The lesion involves the back of the torso · the photograph is a close-up of the affected area.
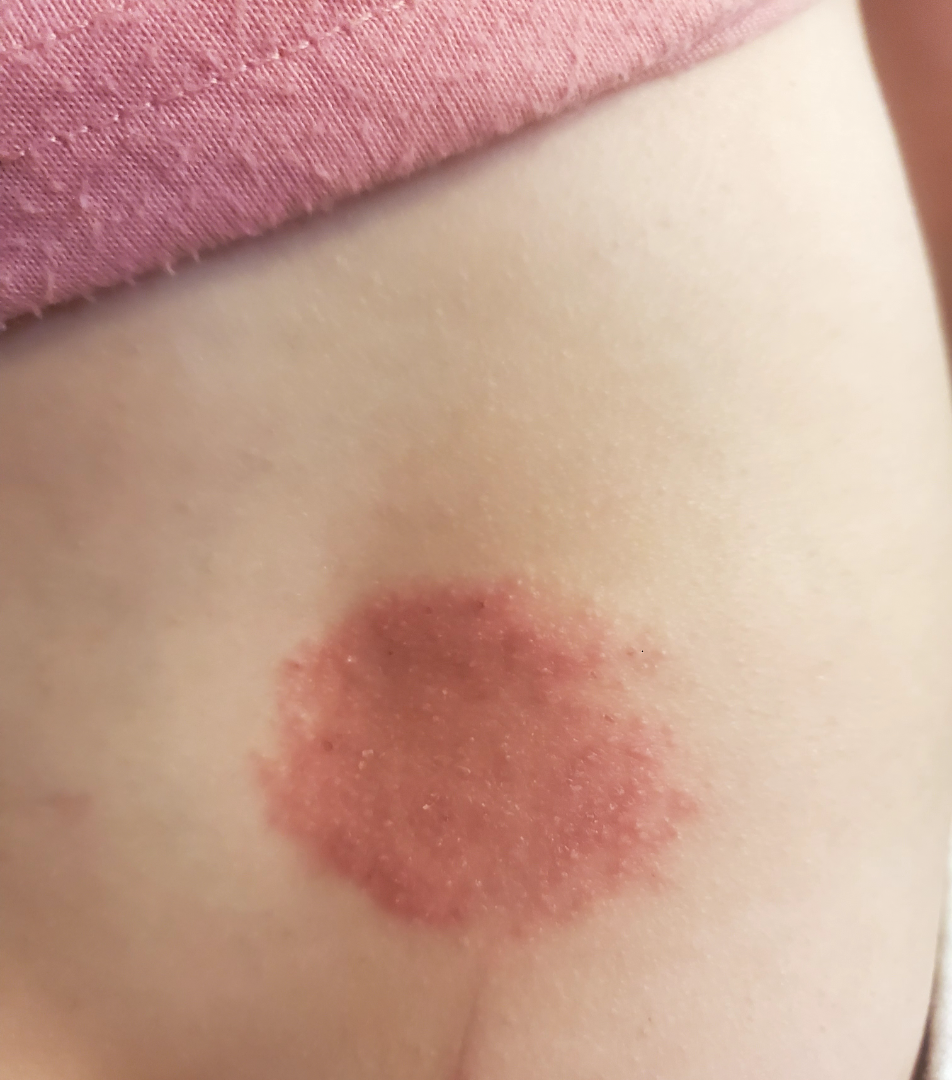differential diagnosis: the leading consideration is Allergic Contact Dermatitis; possibly Acute dermatitis, NOS